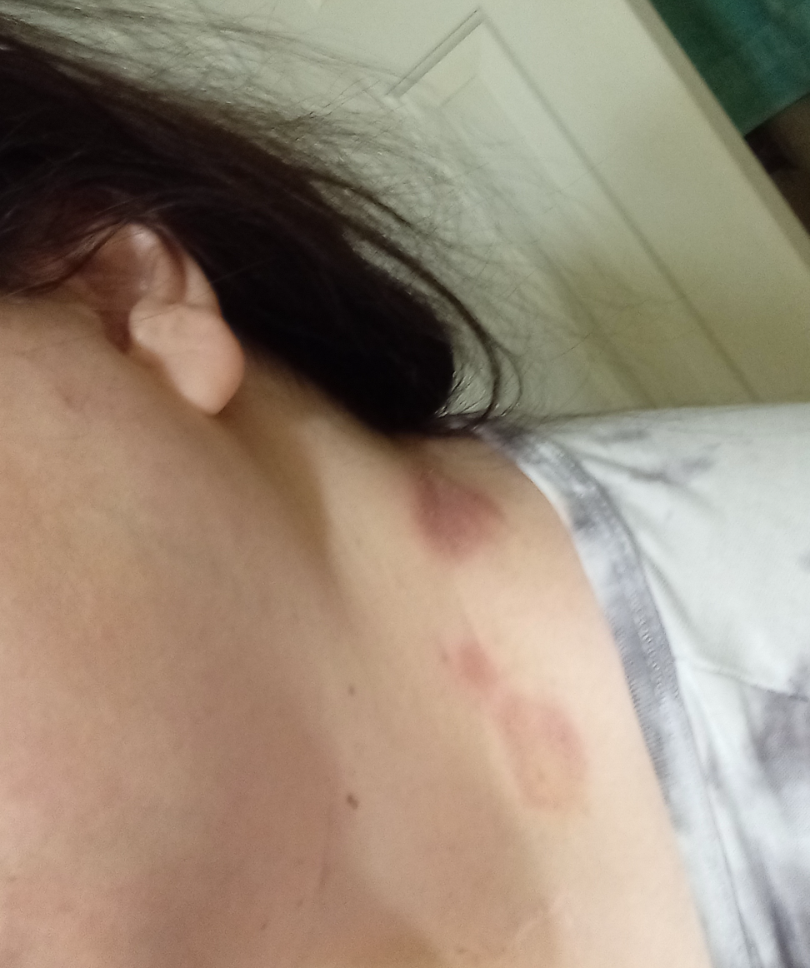| key | value |
|---|---|
| assessment | ungradable on photographic review |
| view | at an angle |
| anatomic site | head or neck |